A dermoscopic photograph of a skin lesion:
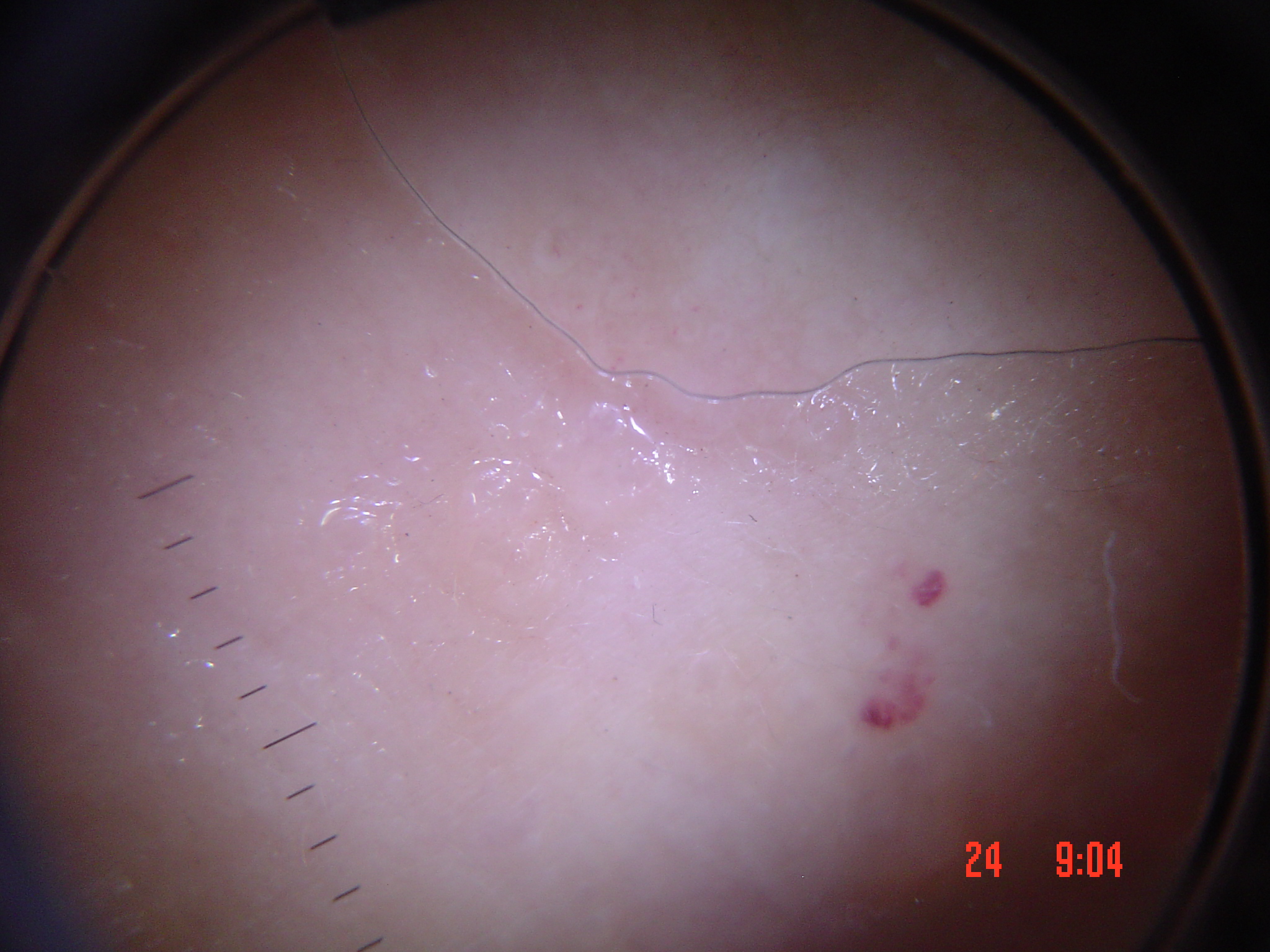The morphology is that of a vascular lesion.
Classified as a hemangioma.